Located on the arm. An image taken at an angle. The subject is 50–59, female: 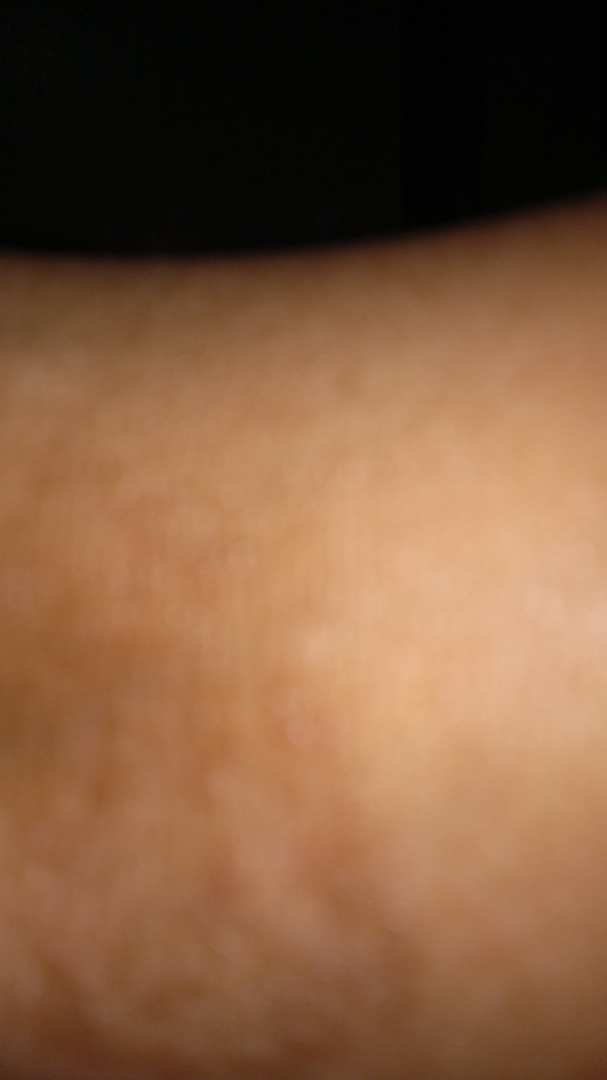<dermatology_case>
<differential>
  <tied_lead>Lichenified eczematous dermatitis, Chronic dermatitis</tied_lead>
  <unlikely>Tinea, Eczema, Post-Inflammatory hyperpigmentation</unlikely>
</differential>
</dermatology_case>